The top or side of the foot is involved; this is a close-up image: 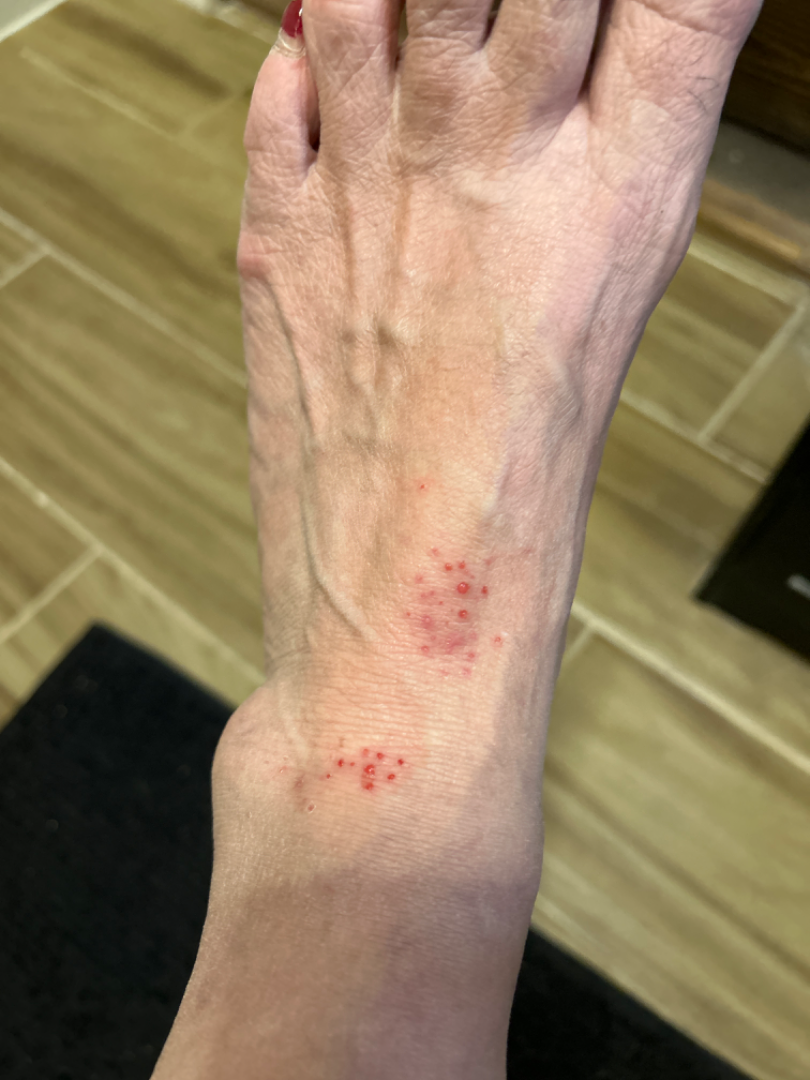The contributor reports the lesion is raised or bumpy and fluid-filled. The contributor reports the condition has been present for more than one year. FST III; lay graders estimated MST 1 (US pool) or 2 (India pool). On photographic review by a dermatologist, the impression was split between Eczema, Insect Bite and Allergic Contact Dermatitis.